A dermoscopy image of a skin lesion. The patient says their skin reddens with sun exposure. A female patient aged 15. Referred for assessment of suspected melanocytic nevus. Few moles overall by the patient's own estimate — 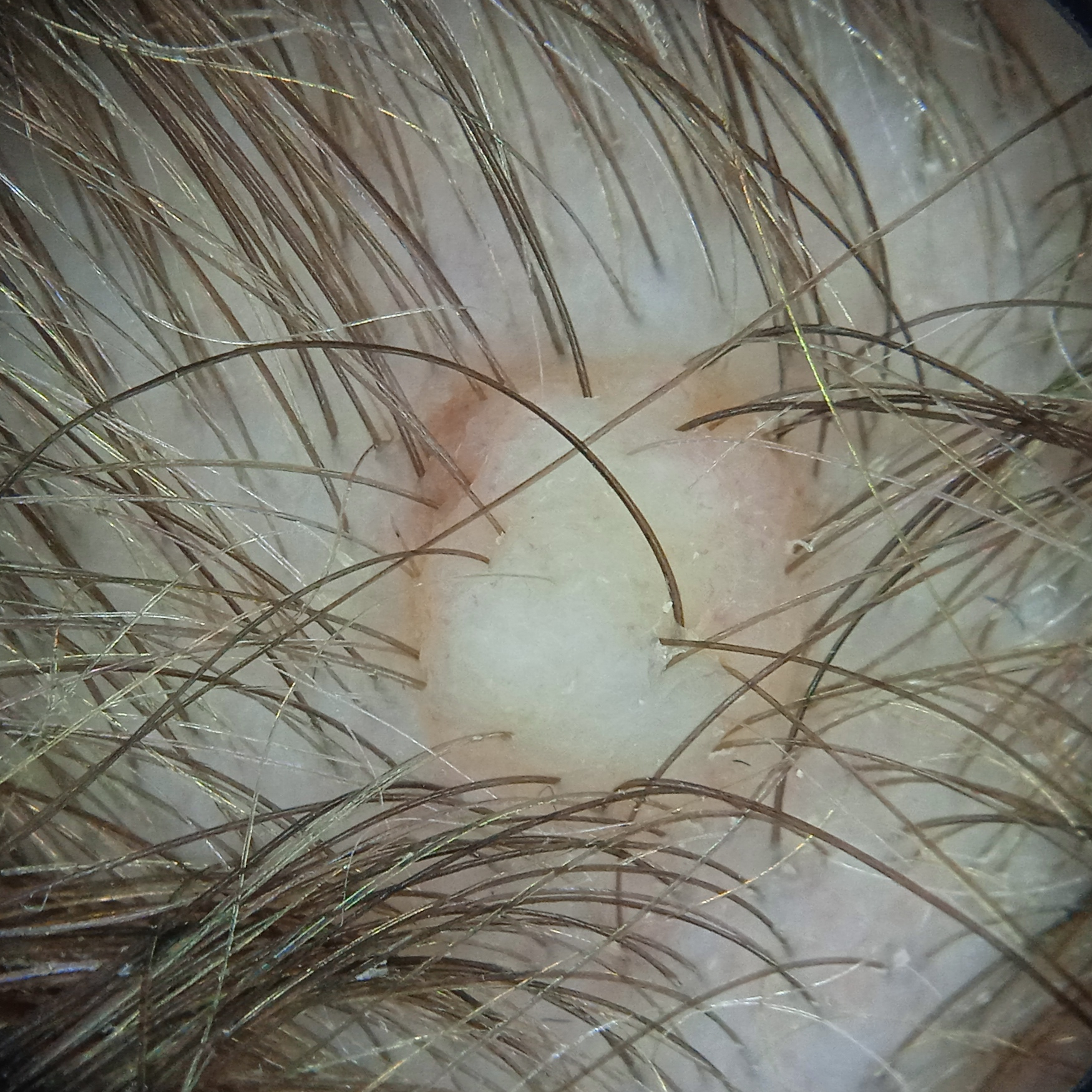Located on the head. The lesion measures approximately 5 mm. The biopsy diagnosis was a melanocytic nevus, following excision.